A male subject aged 73 to 77 · a dermoscopic close-up of a skin lesion: 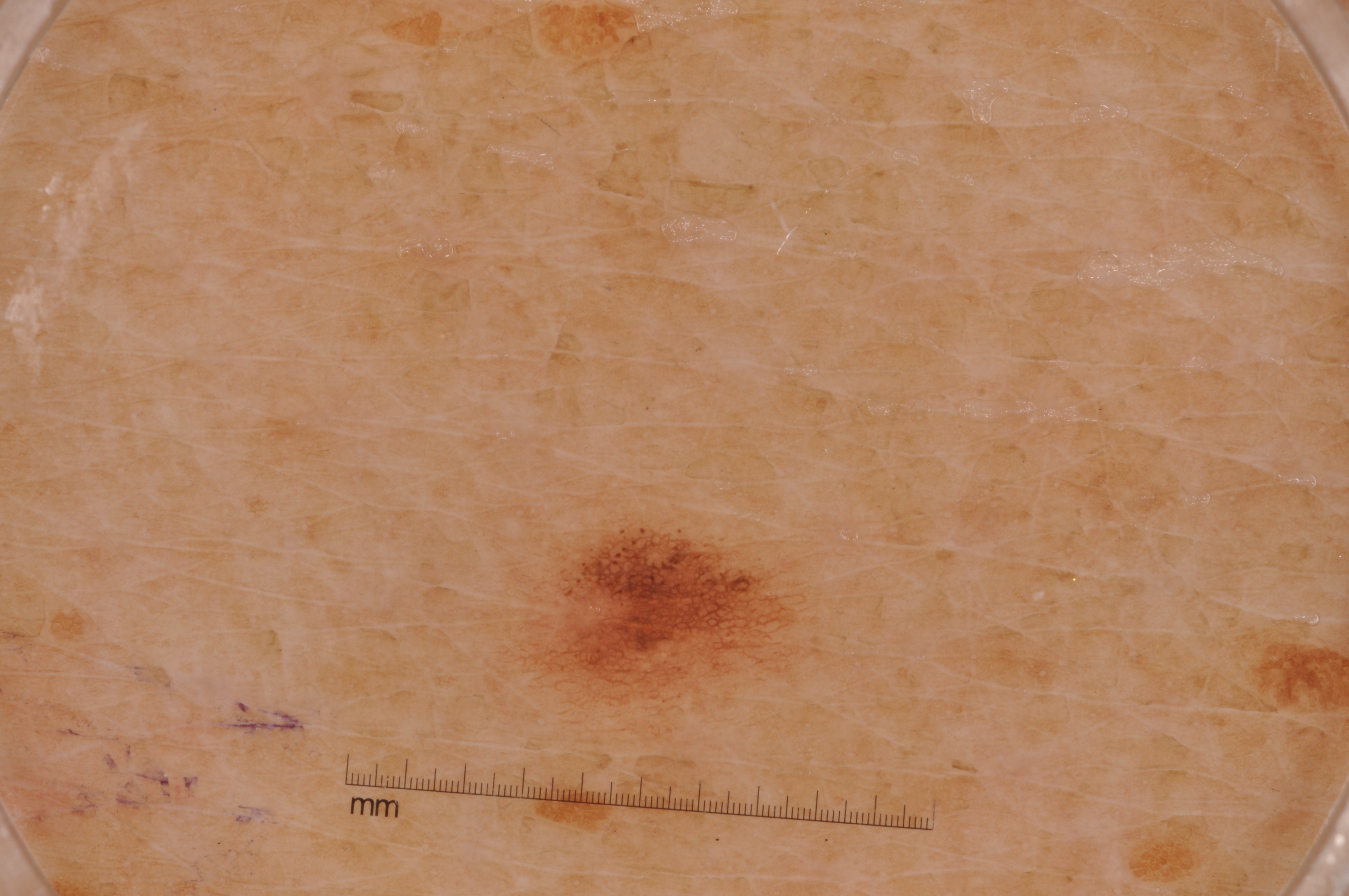On dermoscopy, the lesion shows pigment network. As (left, top, right, bottom), the lesion is located at <bbox>515, 518, 806, 709</bbox>. The lesion covers approximately 3% of the dermoscopic field. The diagnostic assessment was a melanocytic nevus.